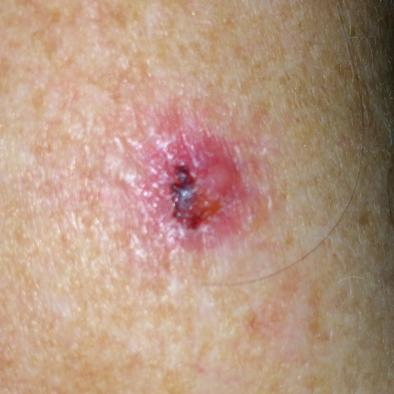image = clinical photo | subject = female, aged 53 | skin type = II | exposures = pesticide exposure, prior malignancy (patient or family), no tobacco use | patient-reported symptoms = elevation, bleeding, growth, itching, pain | pathology = basal cell carcinoma (biopsy-proven).